Lay graders estimated a Monk Skin Tone of 3. Female patient, age 40–49. The patient reports the lesion is raised or bumpy. The lesion is associated with itching. The affected area is the leg. An image taken at an angle. The patient reports the condition has been present for less than one week. The patient reported no systemic symptoms:
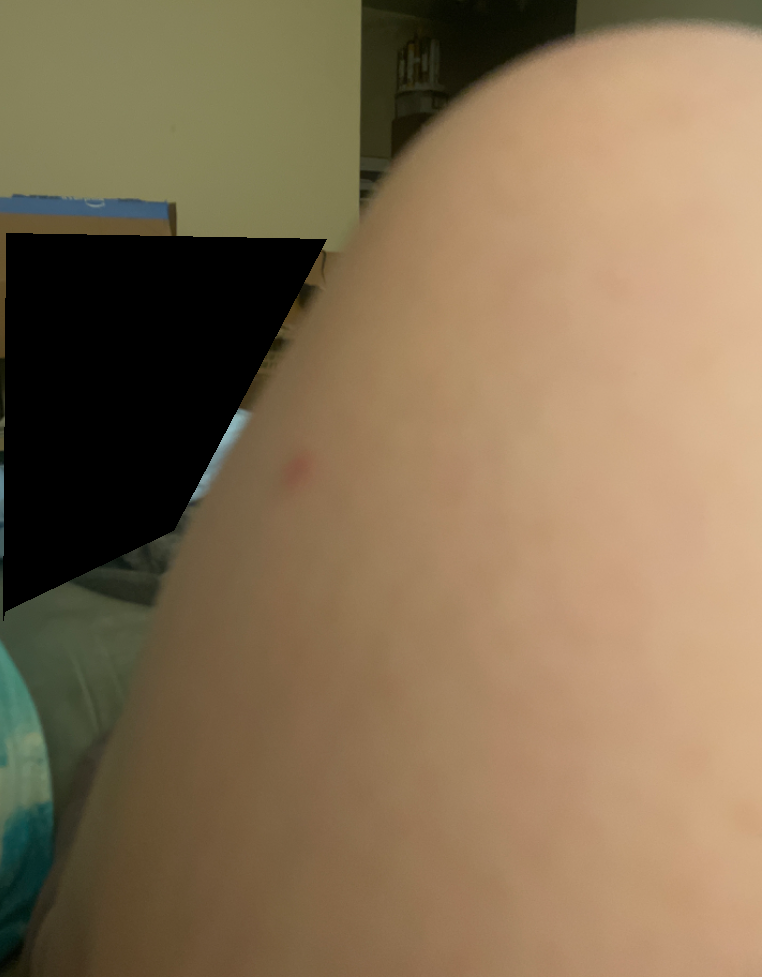  assessment: not assessable